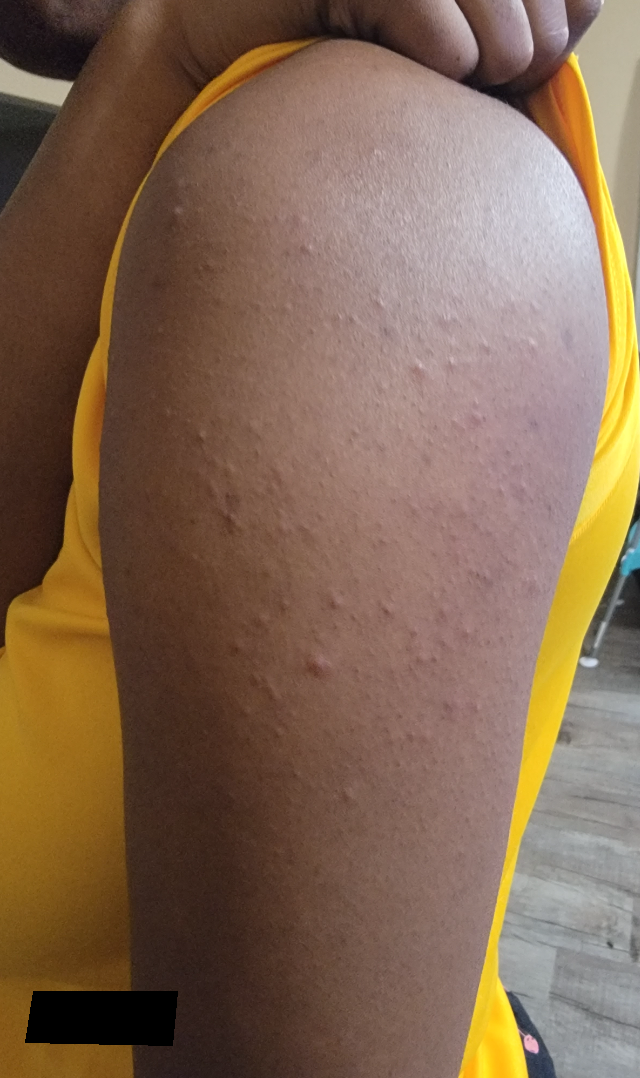History:
The patient reported no systemic symptoms. The lesion involves the arm. The contributor is 18–29, female. The patient described the issue as acne. Texture is reported as raised or bumpy. The patient notes the condition has been present for less than one week. The photograph is a close-up of the affected area. The lesion is associated with itching.
Impression:
Keratosis pilaris (favored); Folliculitis (considered).